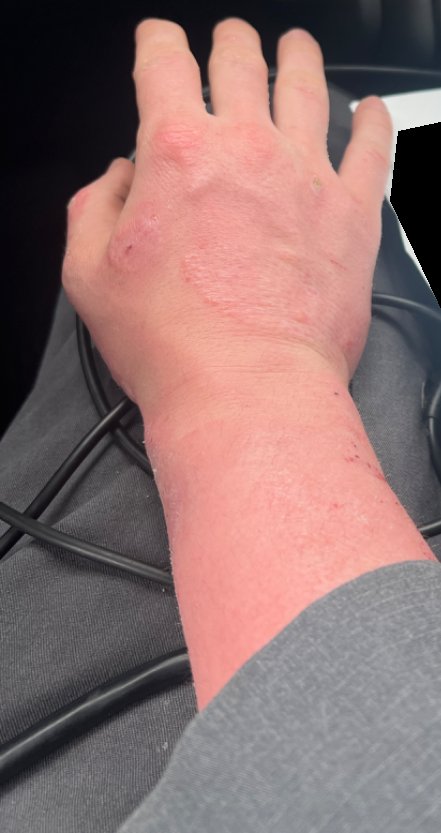Clinical context:
The photo was captured at a distance. The contributor is 18–29, male. The arm is involved.
Assessment:
The reviewing dermatologist's impression was: Tinea and Allergic Contact Dermatitis were considered with similar weight.